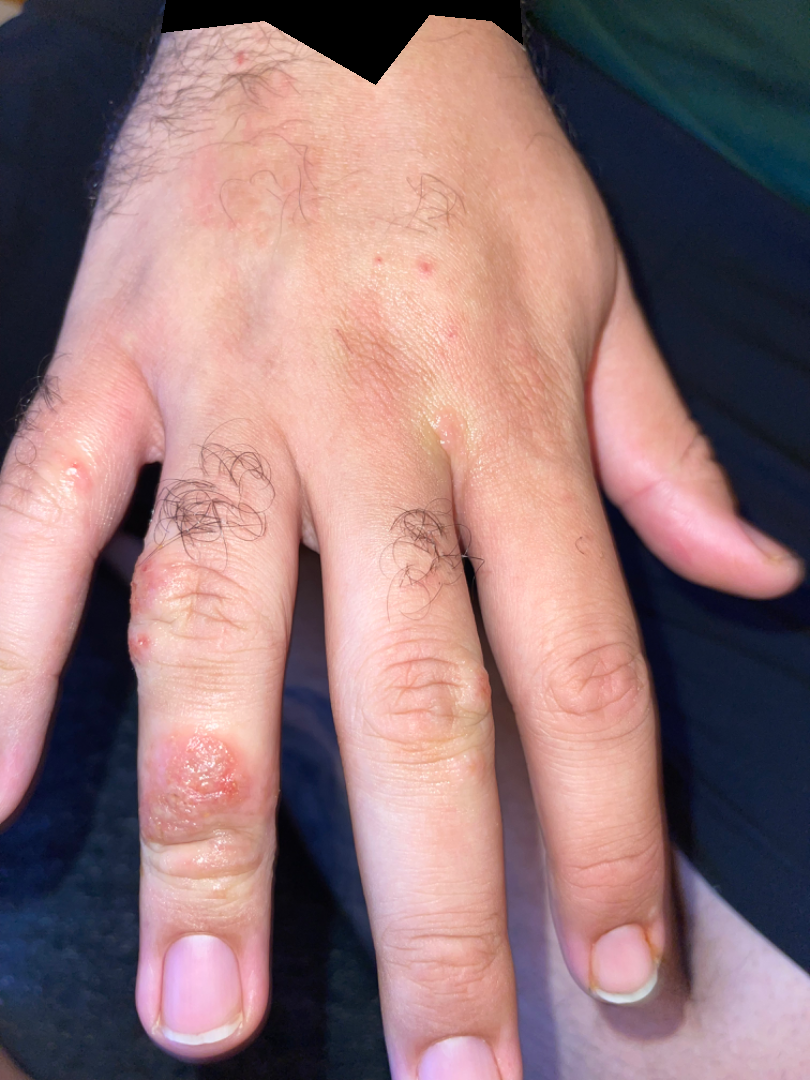assessment: ungradable on photographic review
duration: one to four weeks
body_site:
  - arm
  - head or neck
  - back of the hand
symptoms:
  - bothersome appearance
  - pain
  - itching
  - burning
  - enlargement
shot_type: close-up
skin_tone:
  fitzpatrick: III
  monk_skin_tone:
    - 2
    - 3